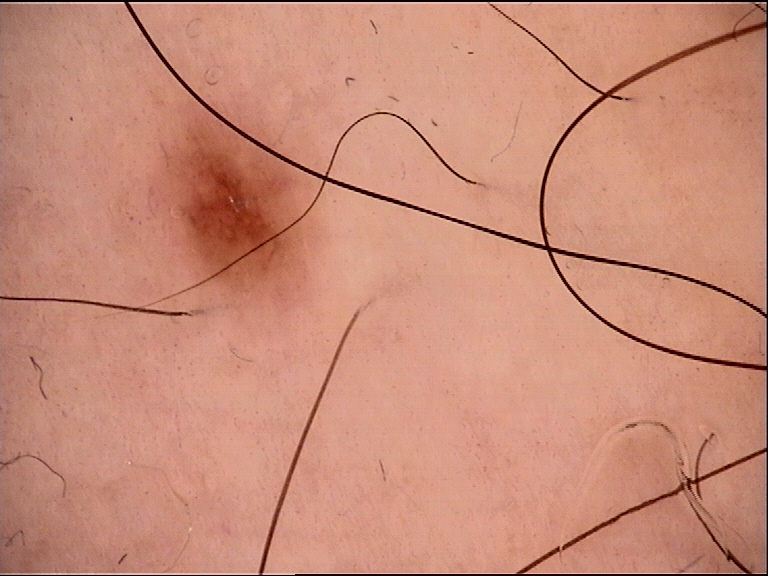{"diagnosis": {"name": "dysplastic junctional nevus", "code": "jd", "malignancy": "benign", "super_class": "melanocytic", "confirmation": "expert consensus"}}